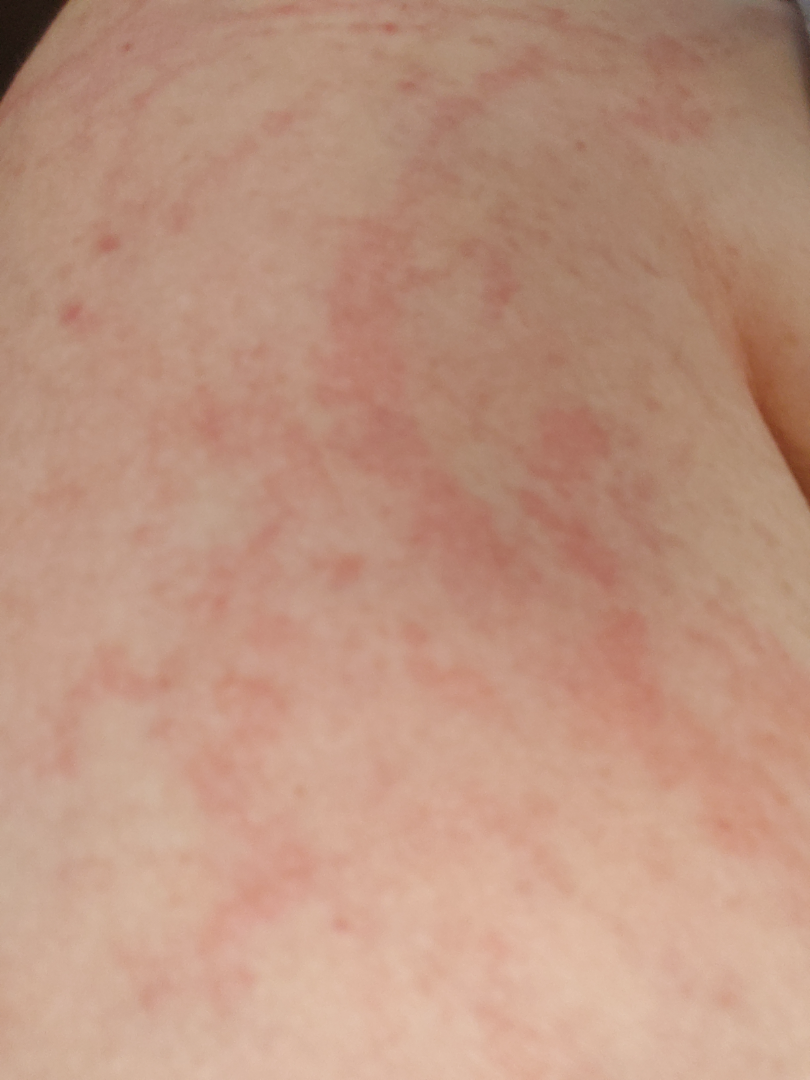Texture is reported as raised or bumpy. The patient notes itching and burning. The affected area is the back of the torso. Close-up view. The patient is a female aged 60–69. The condition has been present for one to three months. Self-categorized by the patient as a rash. Urticaria (leading); Pruritic urticarial papules and plaques of pregnancy (unlikely); Eczema (unlikely); Allergic Contact Dermatitis (unlikely).